This is a dermoscopic photograph of a skin lesion, a female patient about 60 years old.
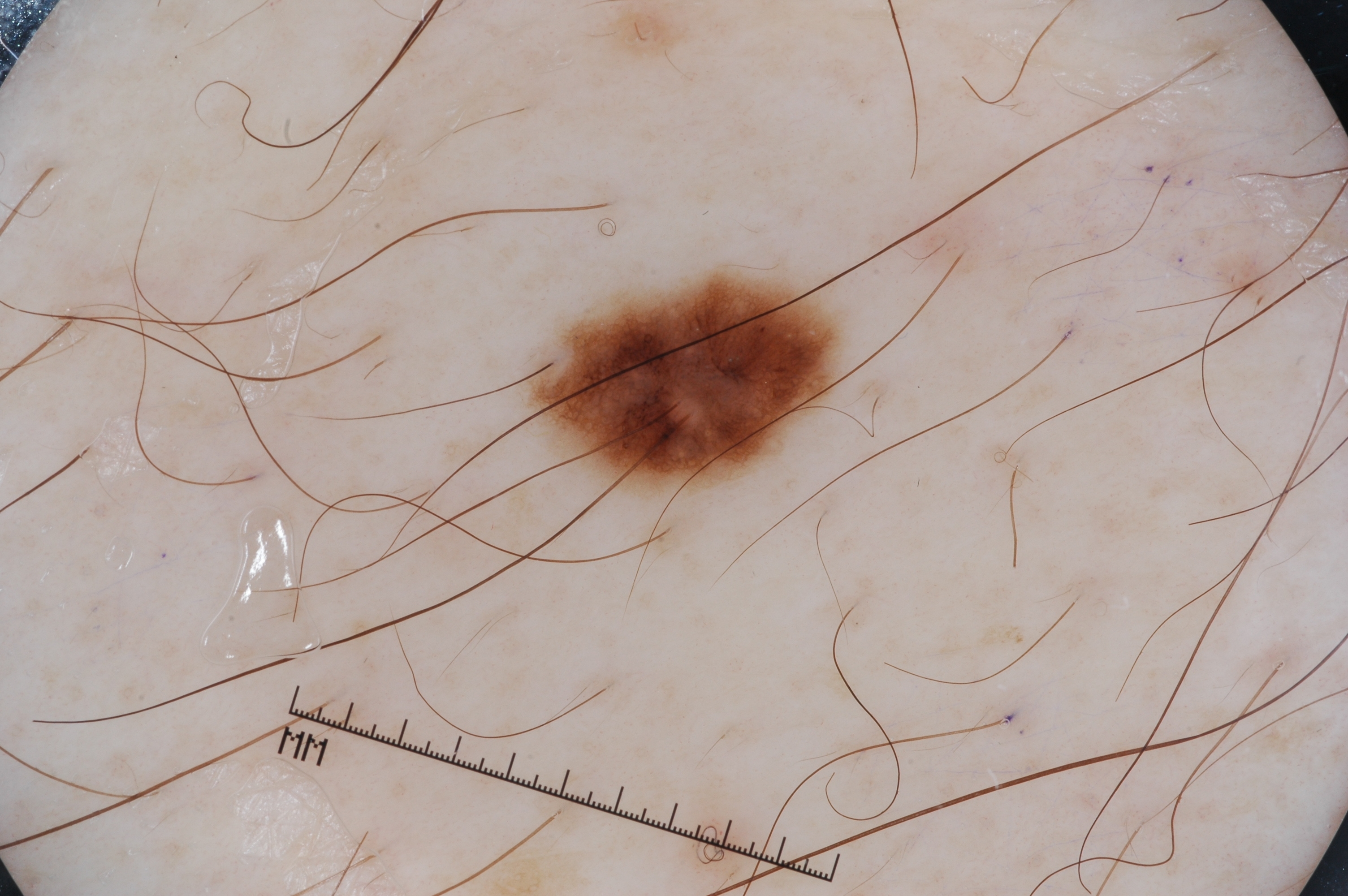{"dermoscopic_features": {"present": ["pigment network", "milia-like cysts"], "absent": ["streaks", "negative network"]}, "lesion_extent": {"approx_field_fraction_pct": 4}, "lesion_location": {"bbox_xyxy": [537, 273, 832, 490]}, "diagnosis": {"name": "melanocytic nevus", "malignancy": "benign", "lineage": "melanocytic", "provenance": "clinical"}}